A subject 65 years of age. A clinical photo of a skin lesion taken with a smartphone:
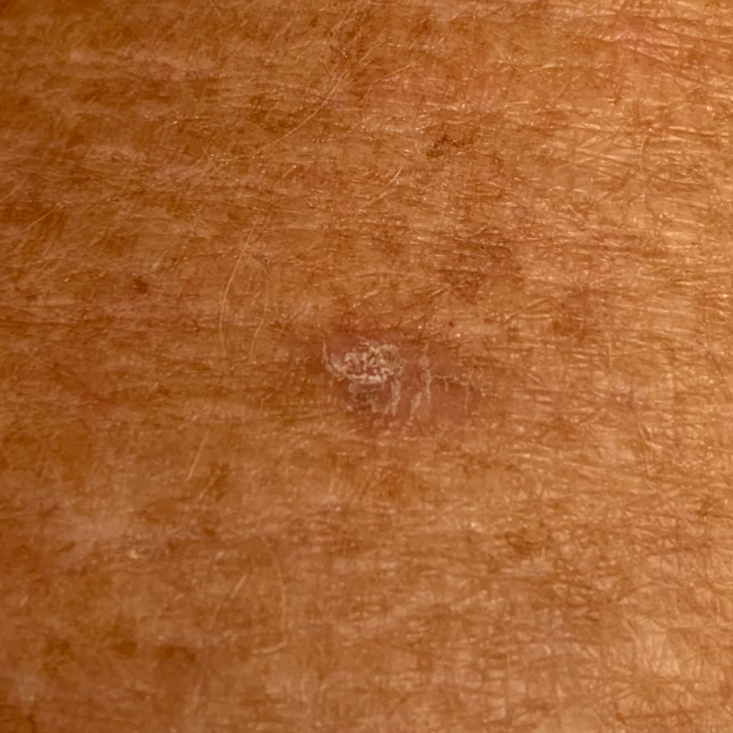Clinical context:
The lesion is on a forearm.
Impression:
The consensus clinical diagnosis was a premalignant lesion — an actinic keratosis.